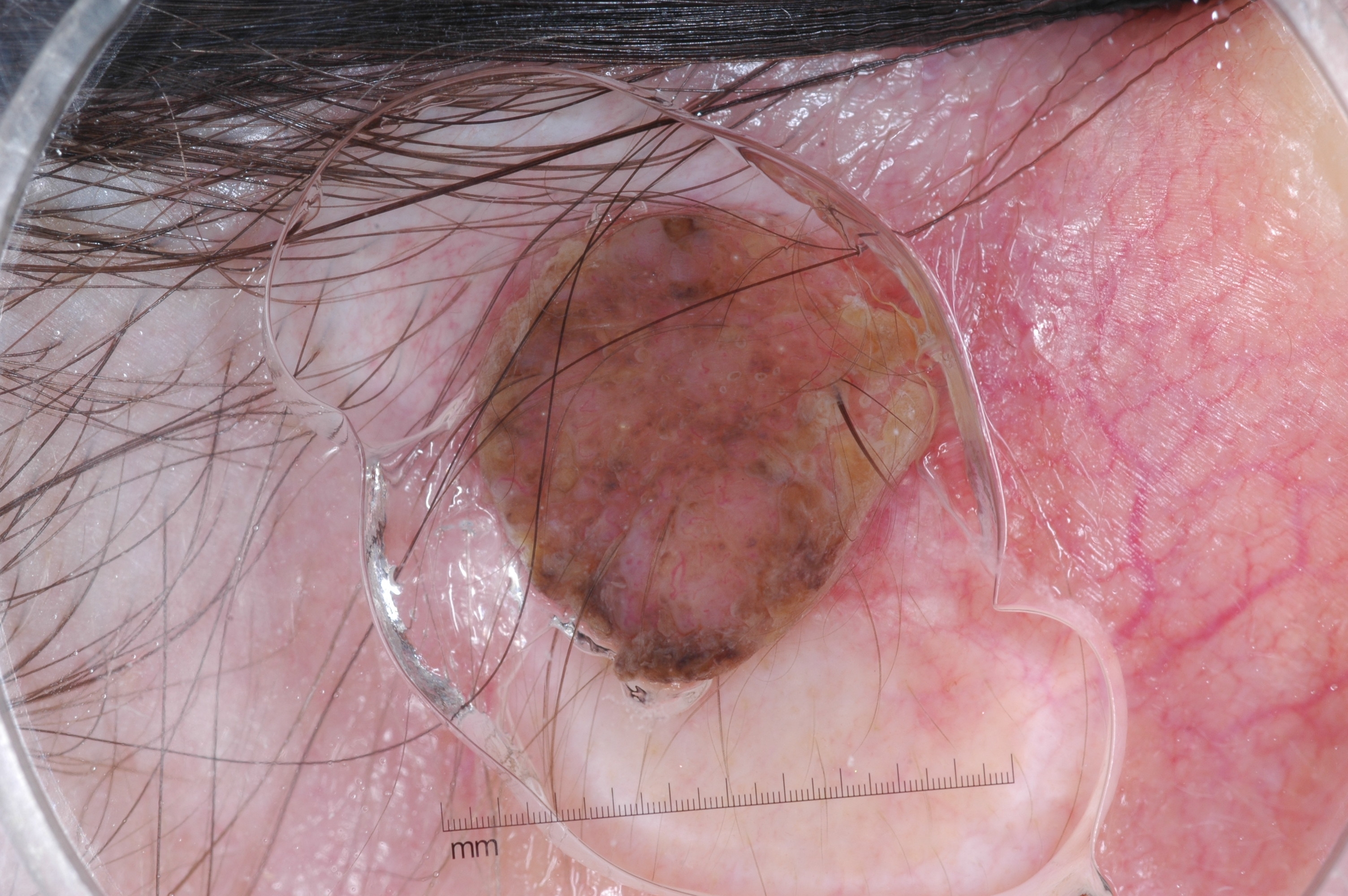Notes:
- modality: dermoscopy
- bounding box: bbox=[466, 202, 939, 684]
- features: milia-like cysts
- lesion size: ~14% of the field
- impression: a melanocytic nevus, a benign lesion